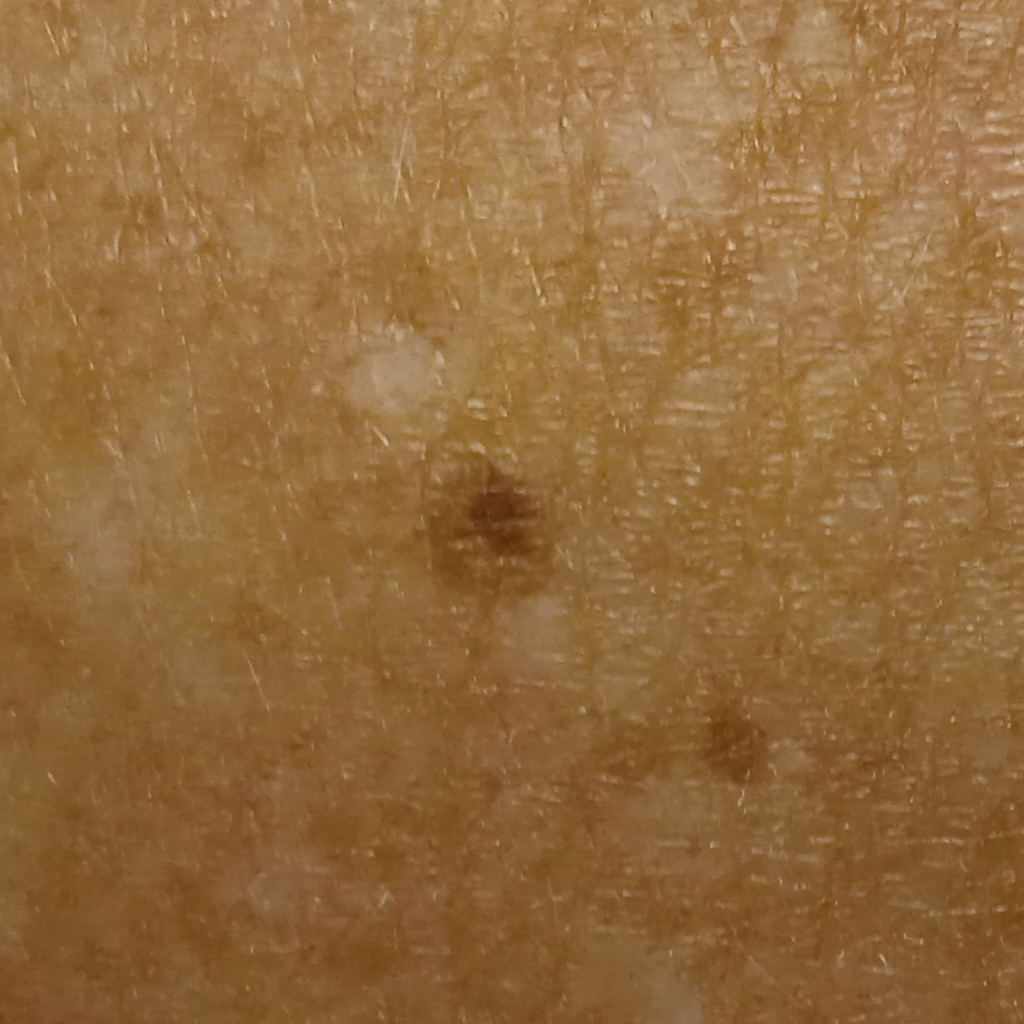Clinical context: A female patient aged 75. The lesion is located on the back. Impression: Dermatologist review favored a melanocytic nevus.